The patient is 40–49, female · the affected area is the back of the hand · this image was taken at a distance — 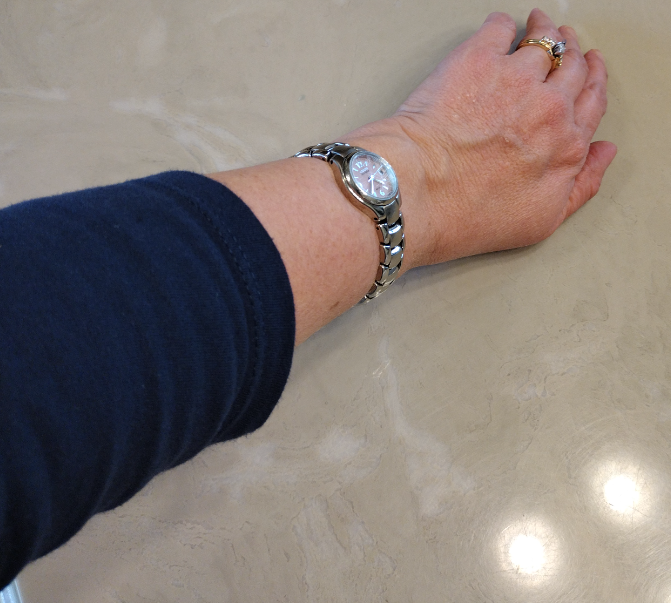Case summary:
– differential diagnosis · Psoriasis (possible); Eczema (possible)